A female subject, in their mid-70s; dermoscopy of a skin lesion.
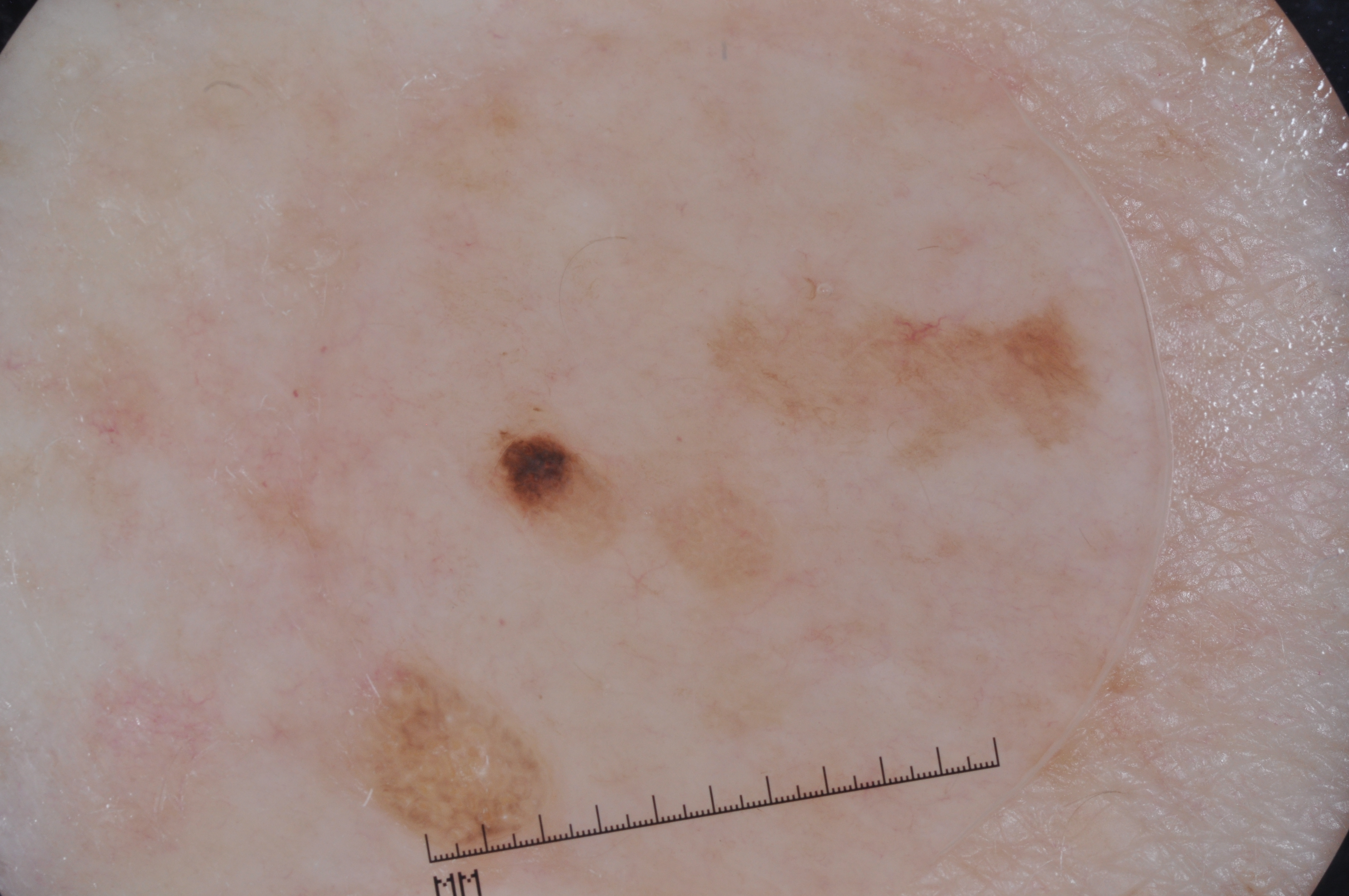<record>
  <dermoscopic_features>
    <present>milia-like cysts</present>
    <absent>streaks, negative network, pigment network</absent>
  </dermoscopic_features>
  <lesion_location>
    <bbox_xyxy>201, 85, 1130, 875</bbox_xyxy>
  </lesion_location>
  <diagnosis>
    <name>seborrheic keratosis</name>
    <malignancy>benign</malignancy>
    <lineage>keratinocytic</lineage>
    <provenance>clinical</provenance>
  </diagnosis>
</record>